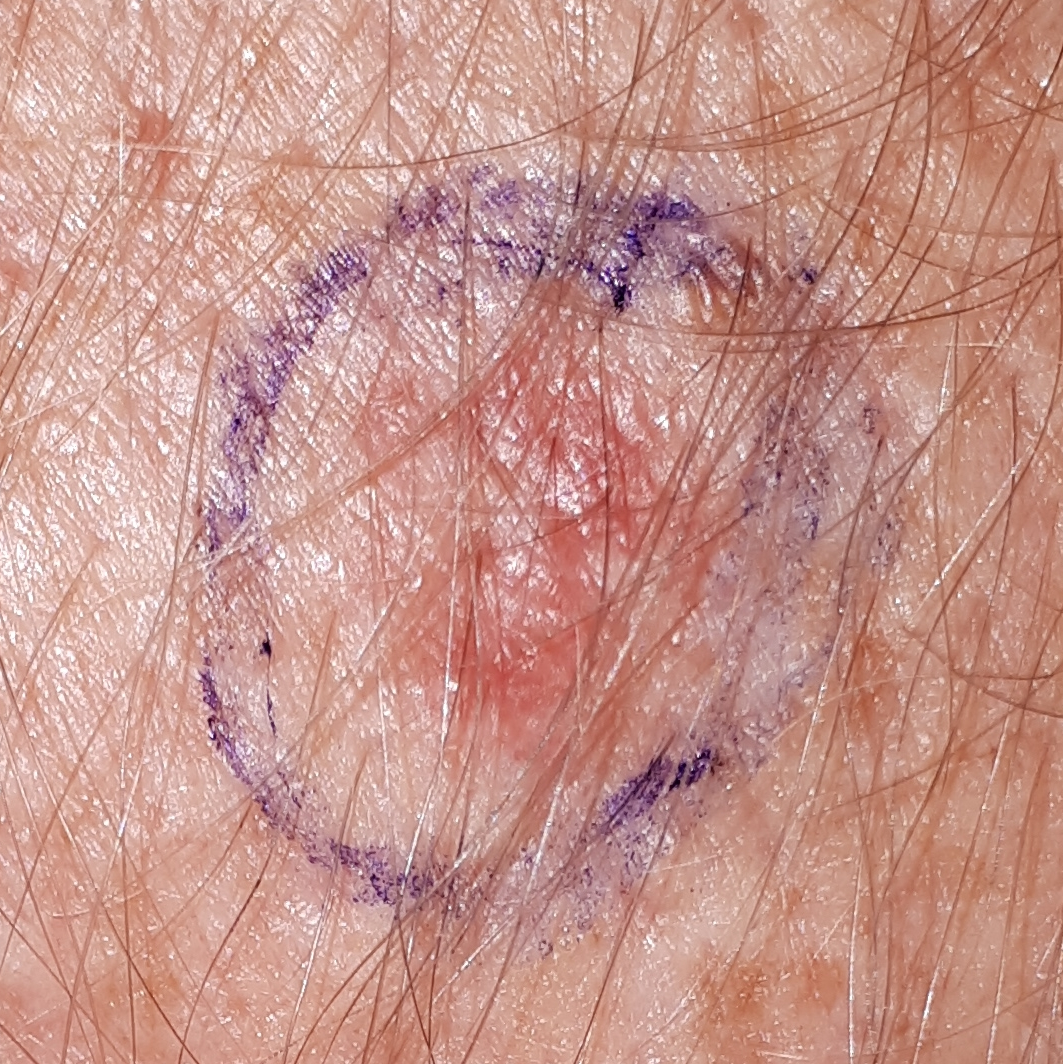A clinical photograph of a skin lesion.
The chart notes prior skin cancer (patient or family), pesticide exposure, prior malignancy (patient or family), and no tobacco use.
A male patient in their 50s.
The lesion is on an arm.
The lesion measures approximately 9 × 6 mm.
Biopsy-confirmed as an actinic keratosis.